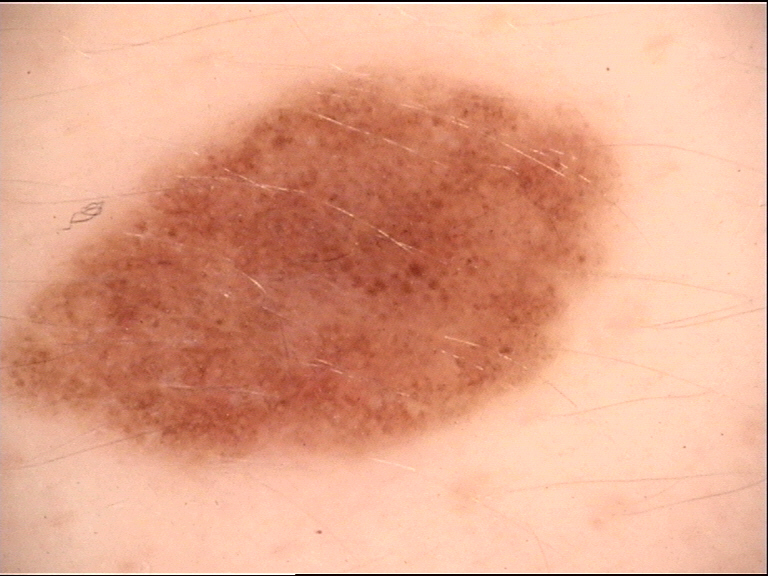Q: What is this lesion?
A: dysplastic compound nevus (expert consensus)